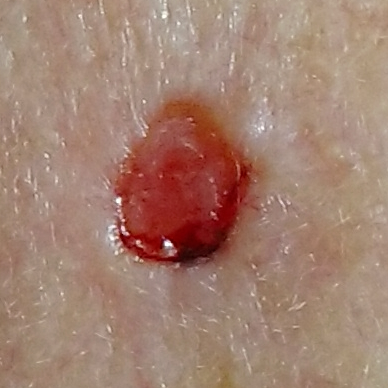exposure history = prior malignancy (patient or family), no prior skin cancer (patient or family) | modality = clinical photo | subject = female, in their early 70s | skin type = III | anatomic site = the face | diameter = 7 × 6 mm | patient-reported symptoms = itching, growth, bleeding, pain | diagnosis = basal cell carcinoma (biopsy-proven).